A subject age 71. A smartphone photograph of a skin lesion:
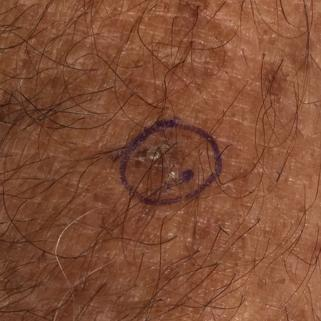Conclusion: The consensus clinical diagnosis was an actinic keratosis.